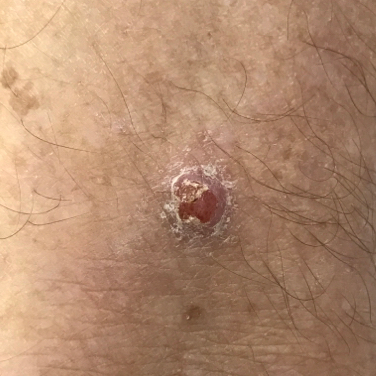{"image": "clinical photograph", "symptoms": {"present": ["elevation", "itching", "bleeding"], "absent": ["pain"]}, "diagnosis": {"name": "squamous cell carcinoma", "code": "SCC", "malignancy": "malignant", "confirmation": "histopathology"}}